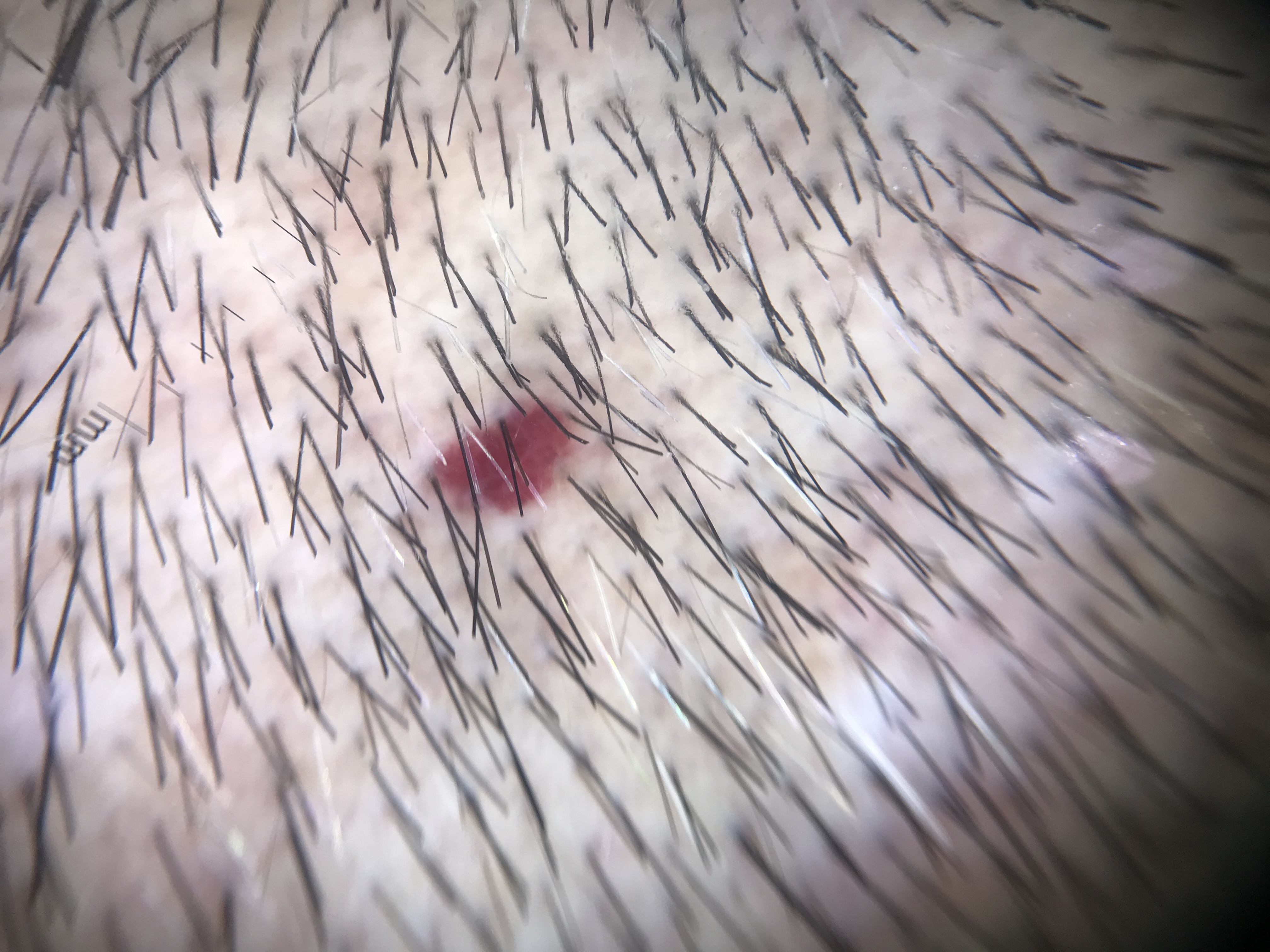* image type · dermoscopy
* category · vascular
* diagnostic label · hemangioma (expert consensus)